Symptoms reported: itching, bothersome appearance and enlargement · the photo was captured at a distance · the contributor is 30–39, female · the lesion is described as raised or bumpy.
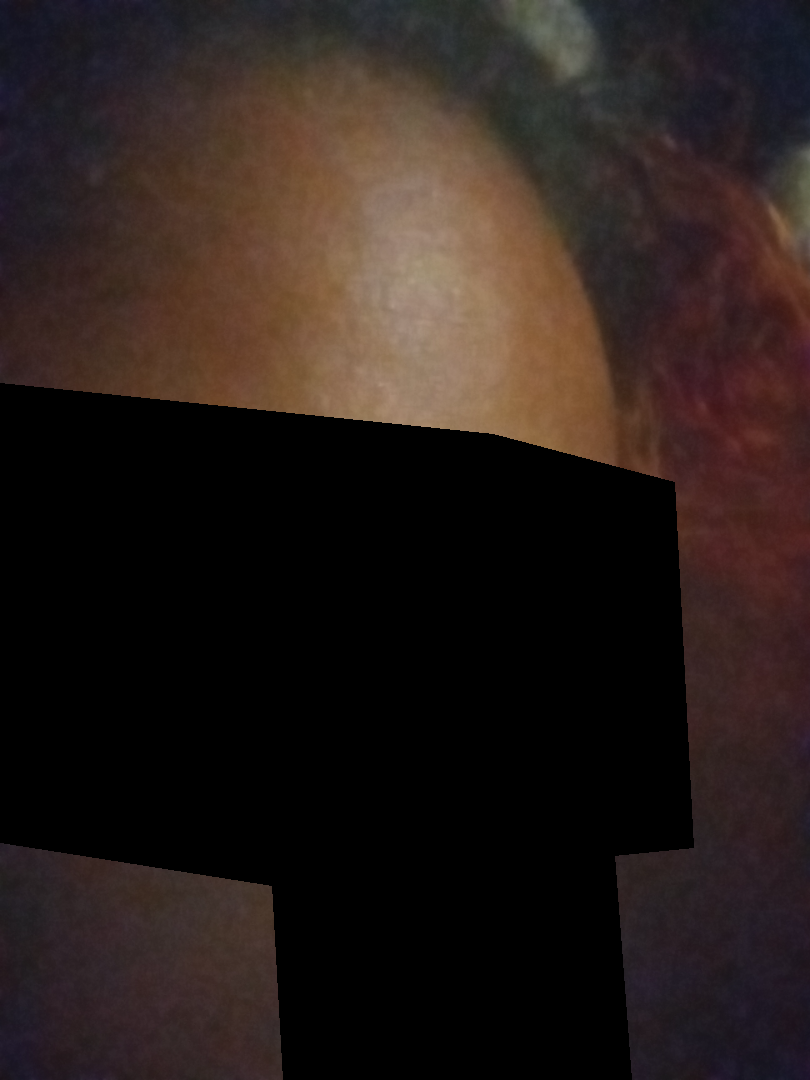<case>
<assessment>indeterminate from the photograph</assessment>
</case>